This image was taken at a distance.
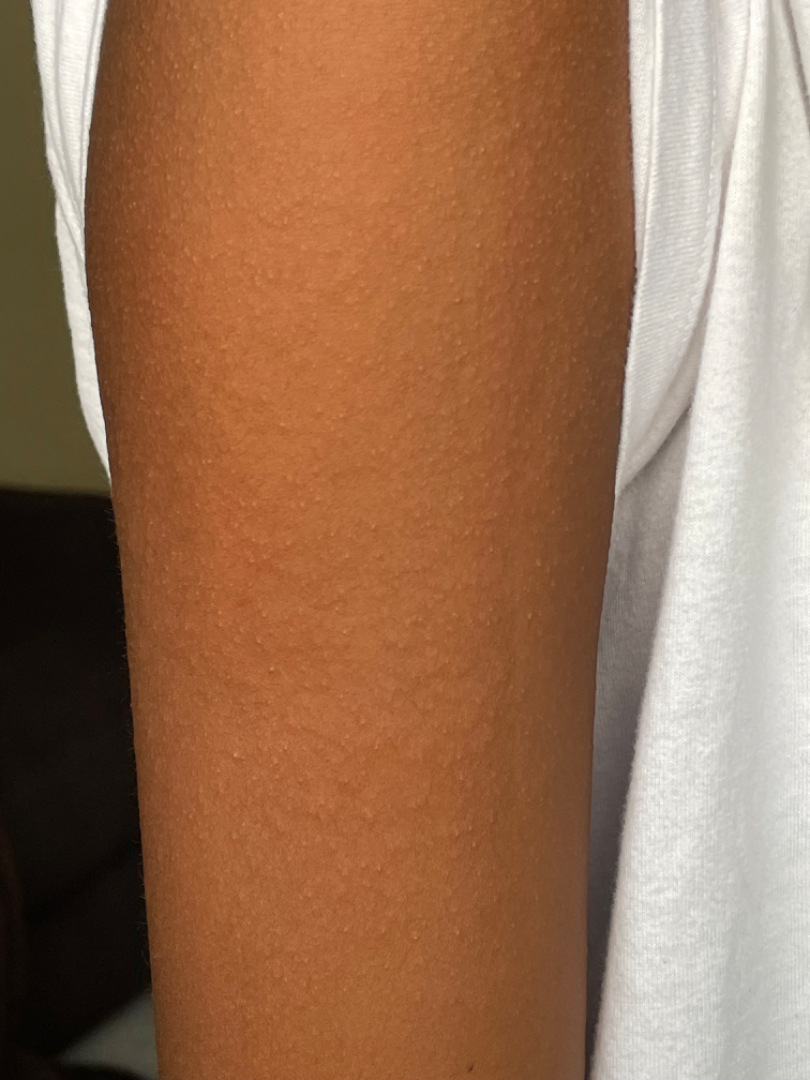Review:
The reviewing dermatologist was unable to assign a differential diagnosis from the image.
Patient information:
Fitzpatrick IV.